The photograph was taken at an angle — 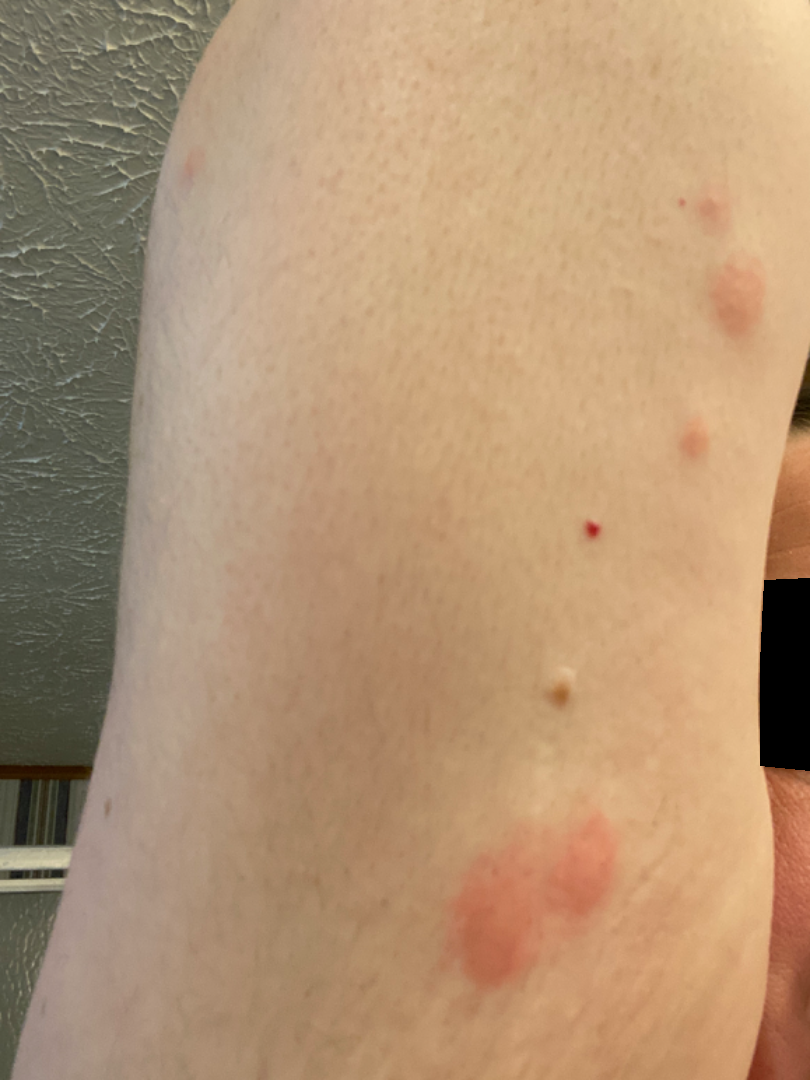differential: Insect Bite (0.50); Inflicted skin lesions (0.50)